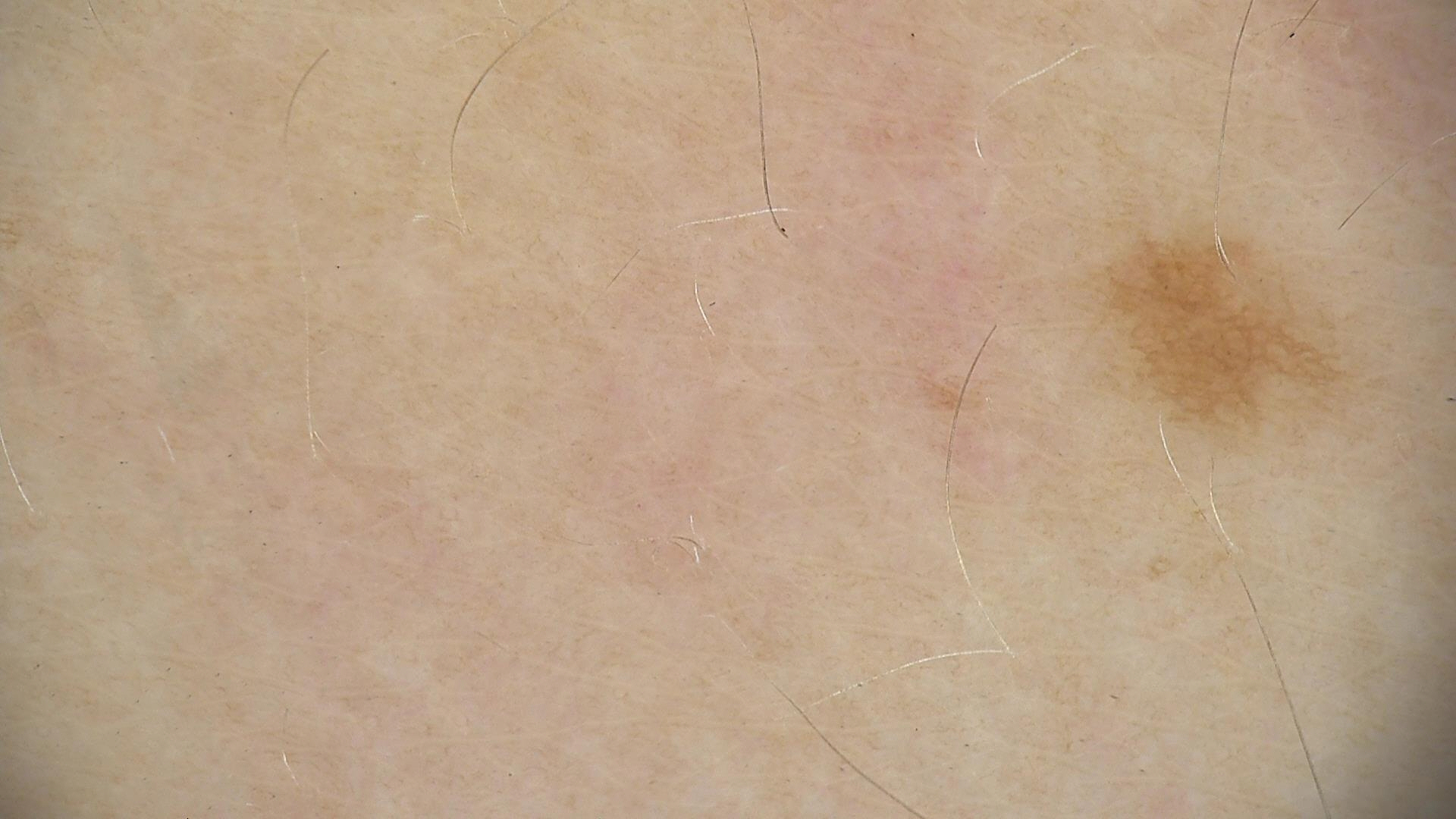Findings:
* assessment · lentigo simplex (expert consensus)